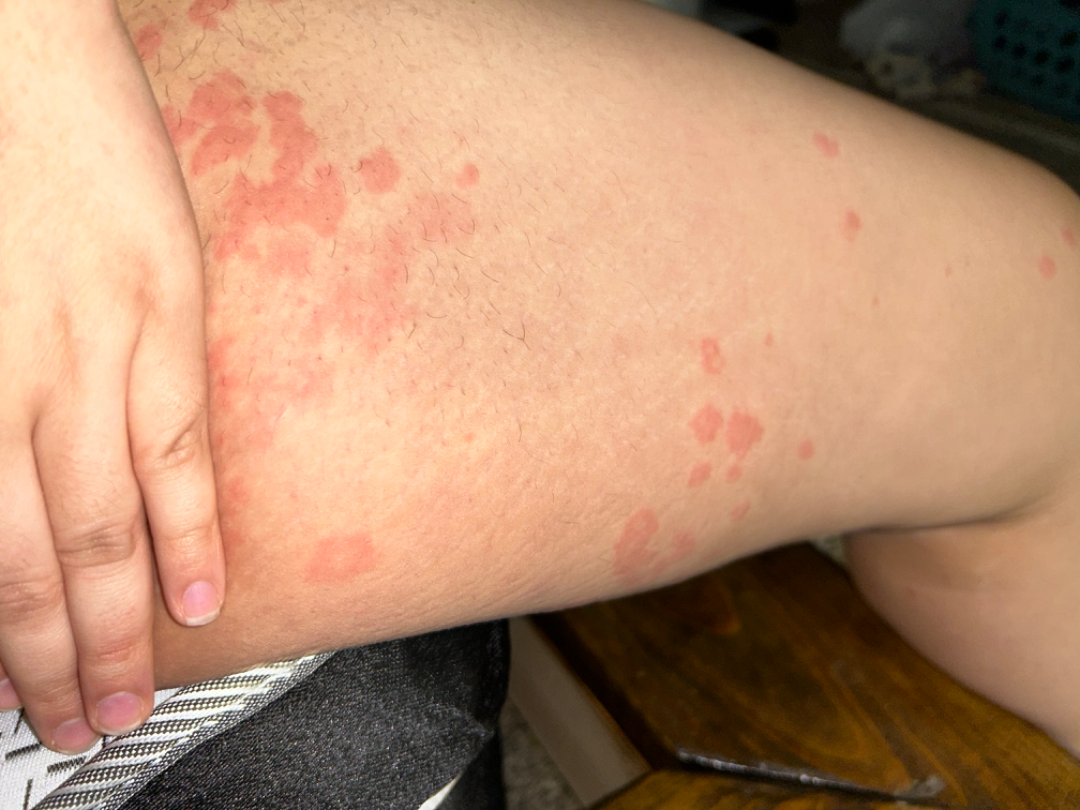Review:
On independent review by the dermatologists: favoring Urticaria; possibly Allergic Contact Dermatitis; less probable is Hypersensitivity.